Dermoscopy of a skin lesion.
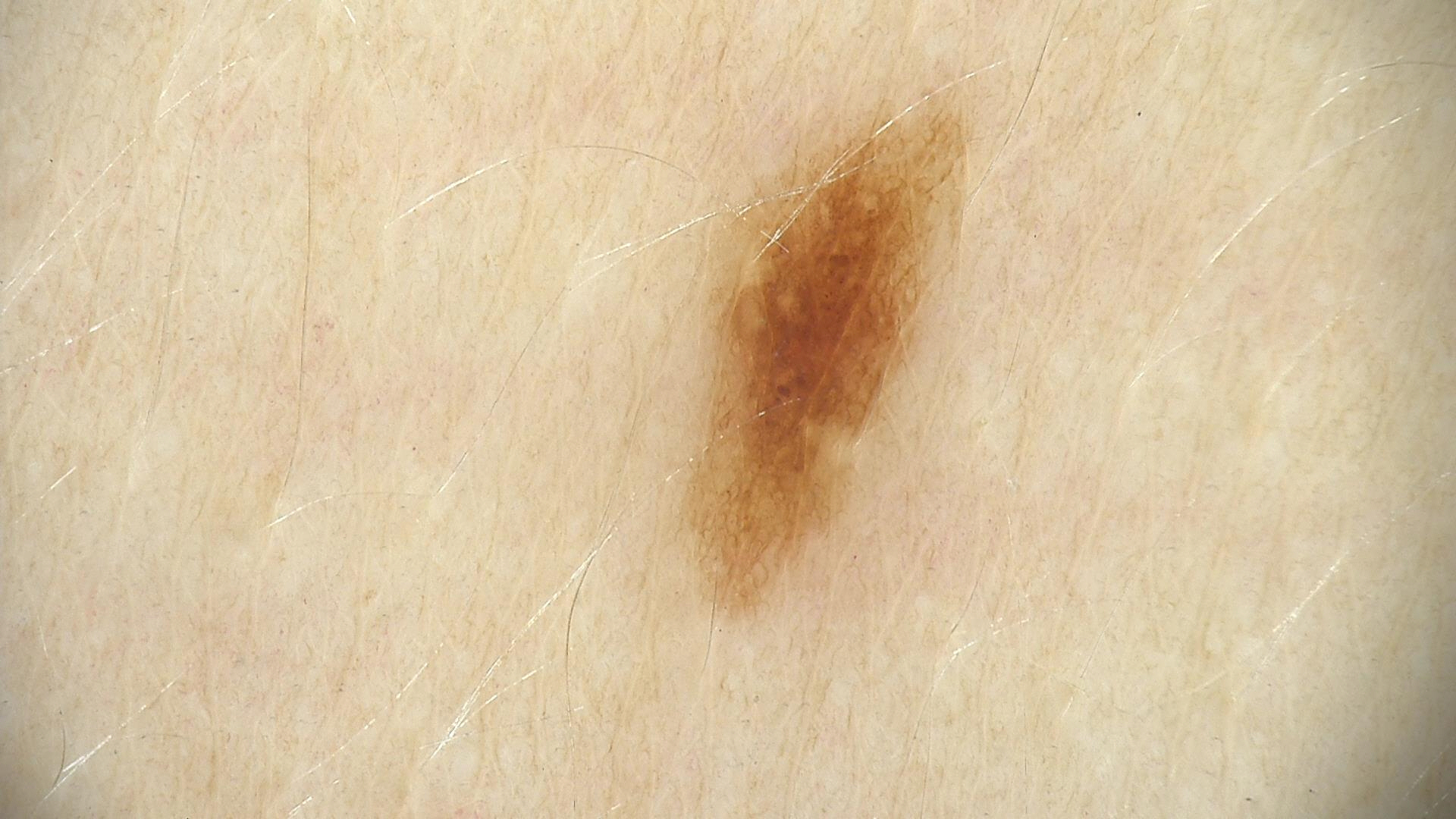diagnosis:
  name: dysplastic junctional nevus
  code: jd
  malignancy: benign
  super_class: melanocytic
  confirmation: expert consensus